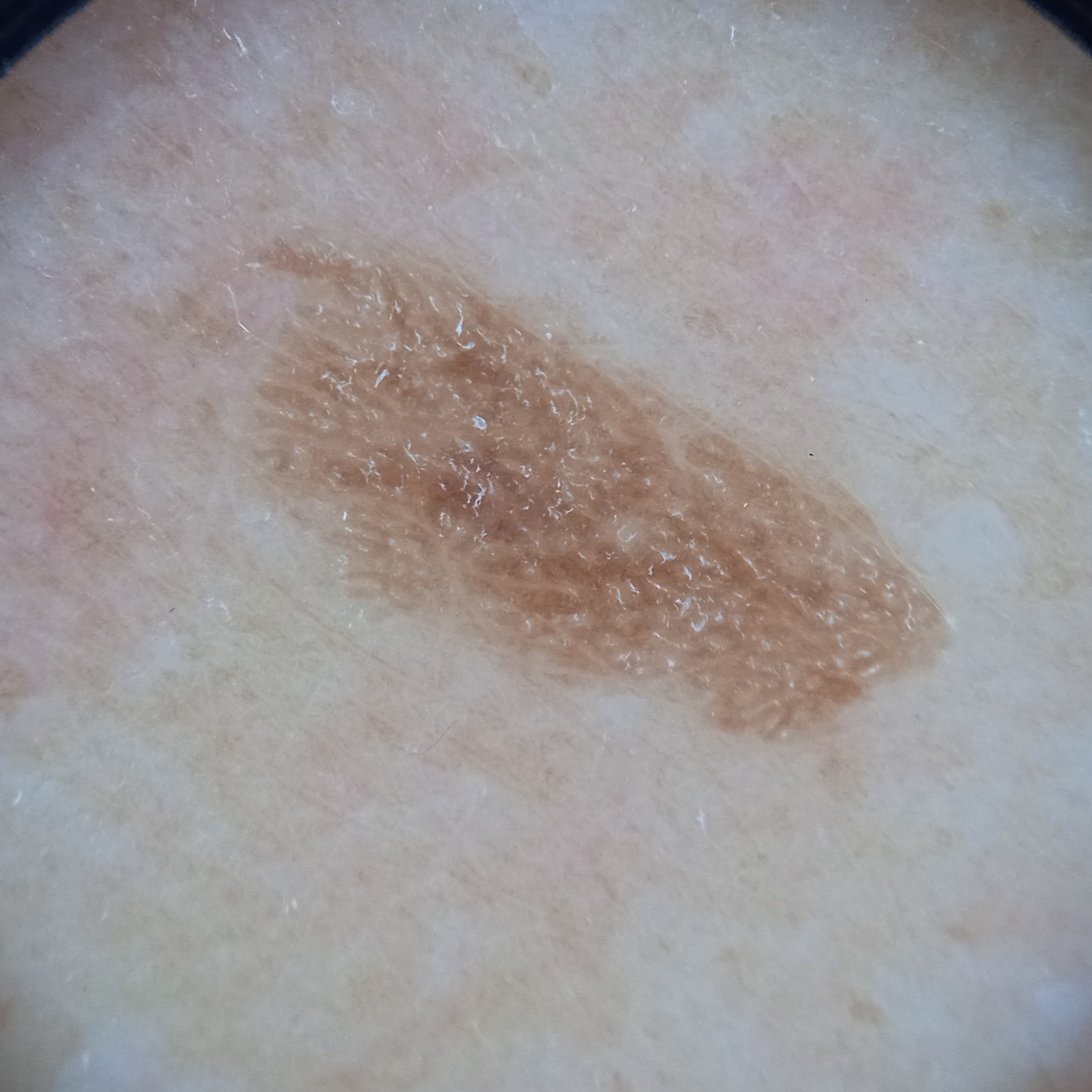Findings:
A skin lesion imaged with a dermatoscope. A female subject 75 years old. Collected as part of a research study, without a referral diagnosis. The patient says their skin tans without first burning. Measuring roughly 8.4 mm.
Impression:
The lesion was assessed as a seborrheic keratosis.